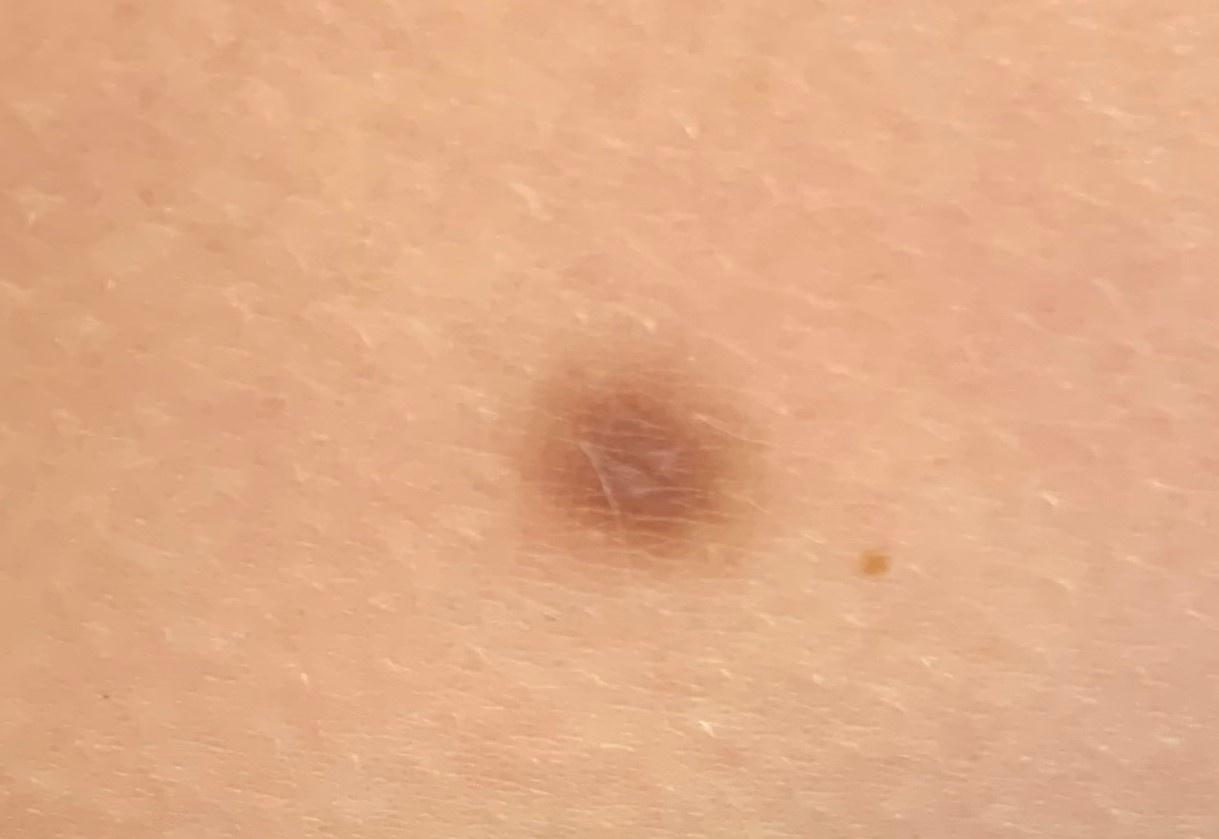| field | value |
|---|---|
| modality | clinical photo (overview) |
| FST | II |
| patient | female, aged approximately 35 |
| diagnosis | Dermatofibroma (clinical impression) |